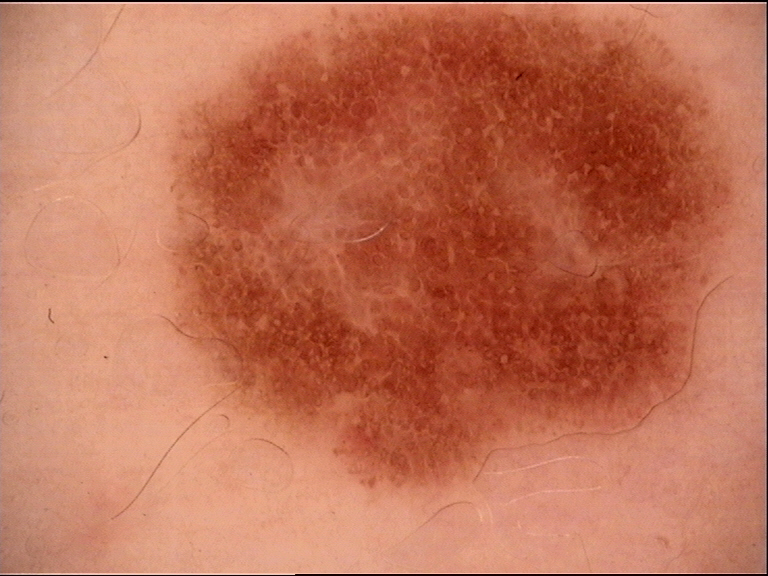The diagnostic label was a dysplastic junctional nevus.